A clinical photo of a skin lesion taken with a smartphone · a male patient in their 50s:
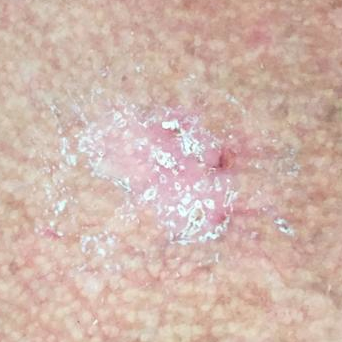{"lesion_location": "the chest", "symptoms": {"present": ["itching", "elevation", "pain"], "absent": ["change in appearance", "growth"]}, "diagnosis": {"name": "basal cell carcinoma", "code": "BCC", "malignancy": "malignant", "confirmation": "histopathology"}}